Few moles overall by the patient's own estimate; on a questionnaire the patient reported a personal history of cancer, a family history of skin cancer, no immunosuppression, and no personal history of skin cancer; the referring clinician suspected basal cell carcinoma: 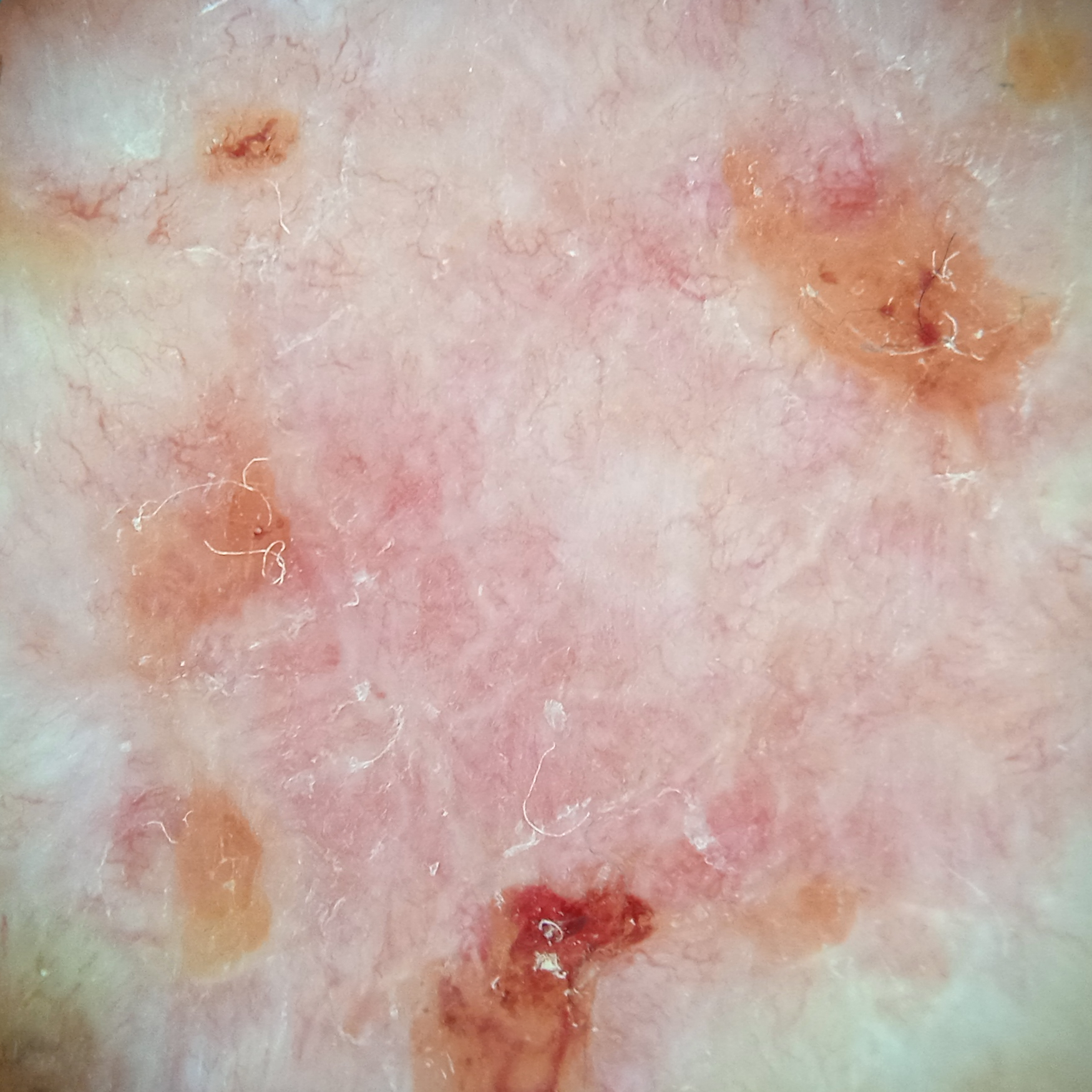The lesion is located on the back. Measuring roughly 12.6 mm. Confirmed on histopathology as a basal cell carcinoma, following excision, with a measured tumor thickness of 3 mm.